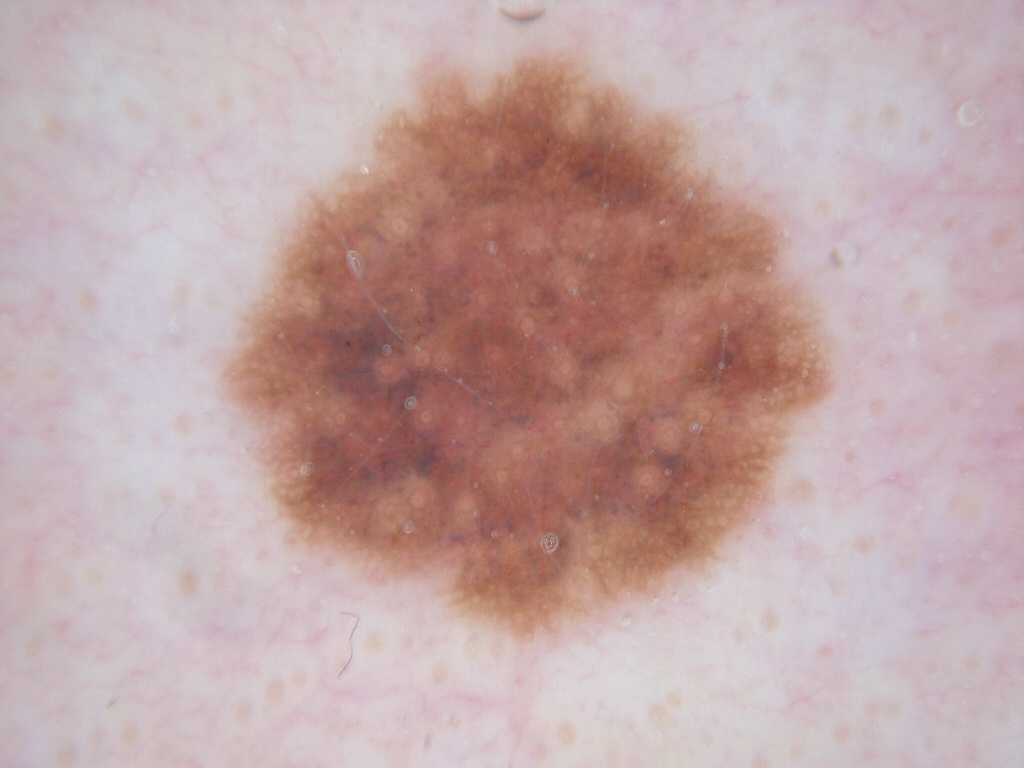The patient is a female aged 33-37. A dermatoscopic image of a skin lesion. Dermoscopic review identifies pigment network. As (left, top, right, bottom), lesion location: 223 49 834 636. The lesion occupies roughly 31% of the field. The diagnostic assessment was a melanocytic nevus.